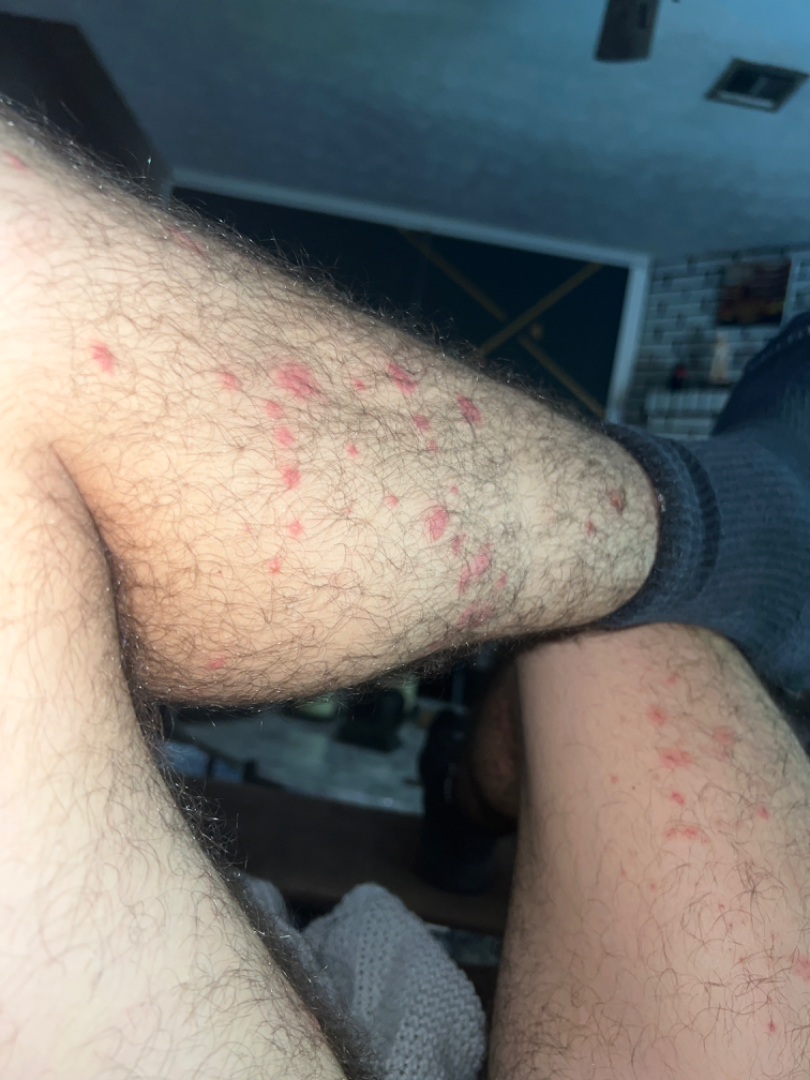The lesion involves the leg. This image was taken at an angle. In keeping with Insect Bite.